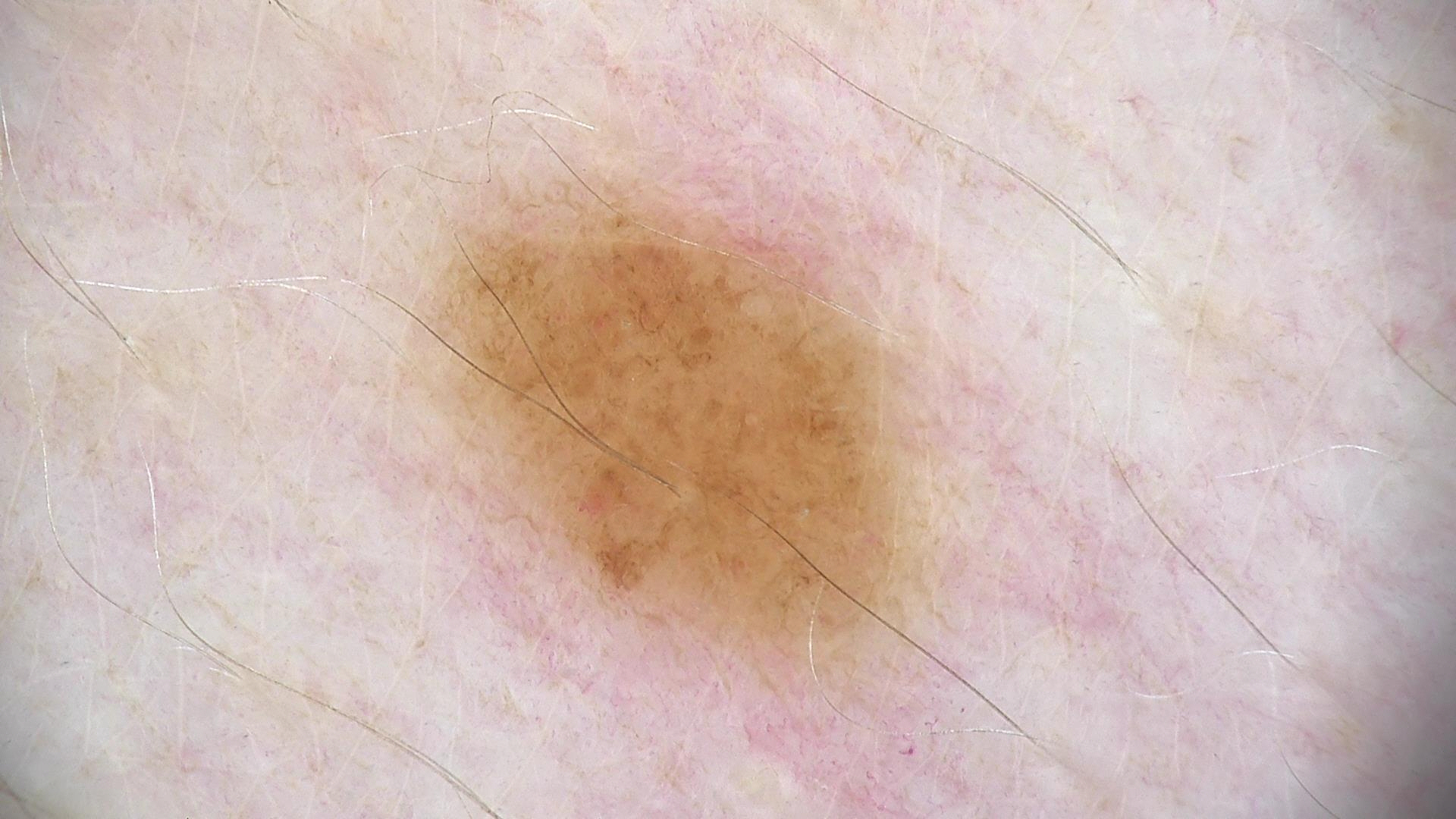A dermoscopic image of a skin lesion. Labeled as a dysplastic junctional nevus.